This is a close-up image. The subject is 18–29, female. The lesion involves the front of the torso — 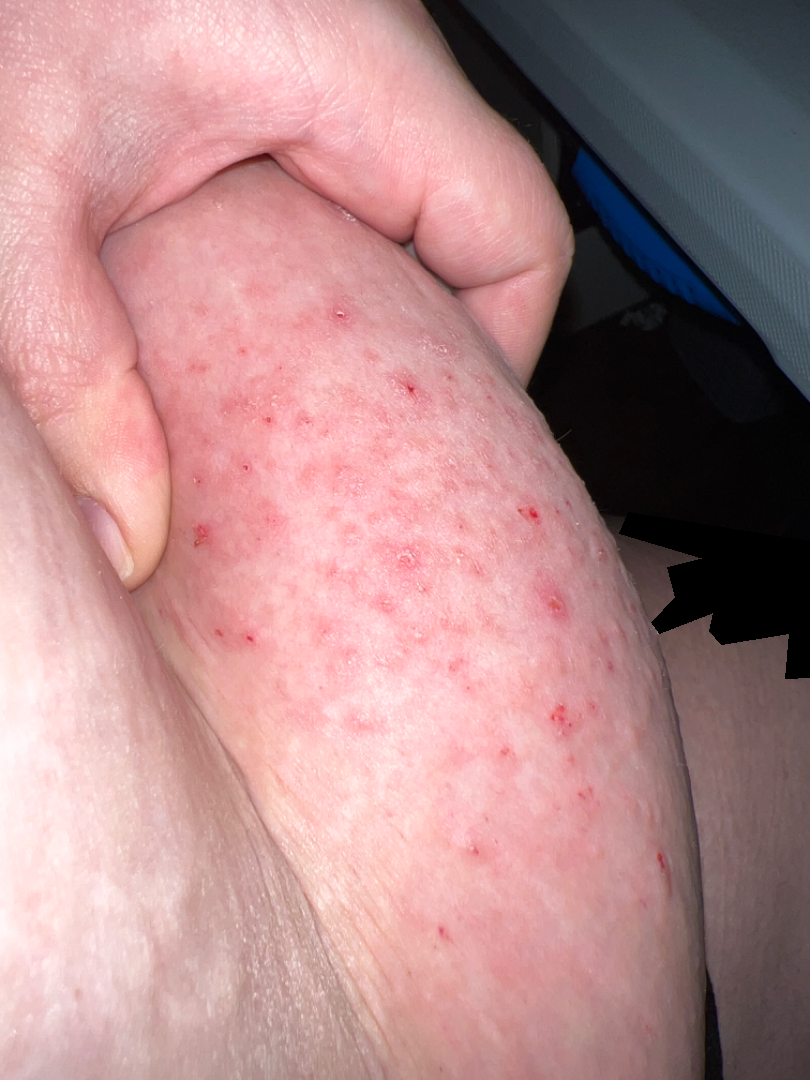The lesion is described as raised or bumpy. FST I; lay graders estimated 2 on the MST. Symptoms reported: itching. The patient considered this a rash. No relevant systemic symptoms. On dermatologist assessment of the image, most consistent with Eczema.